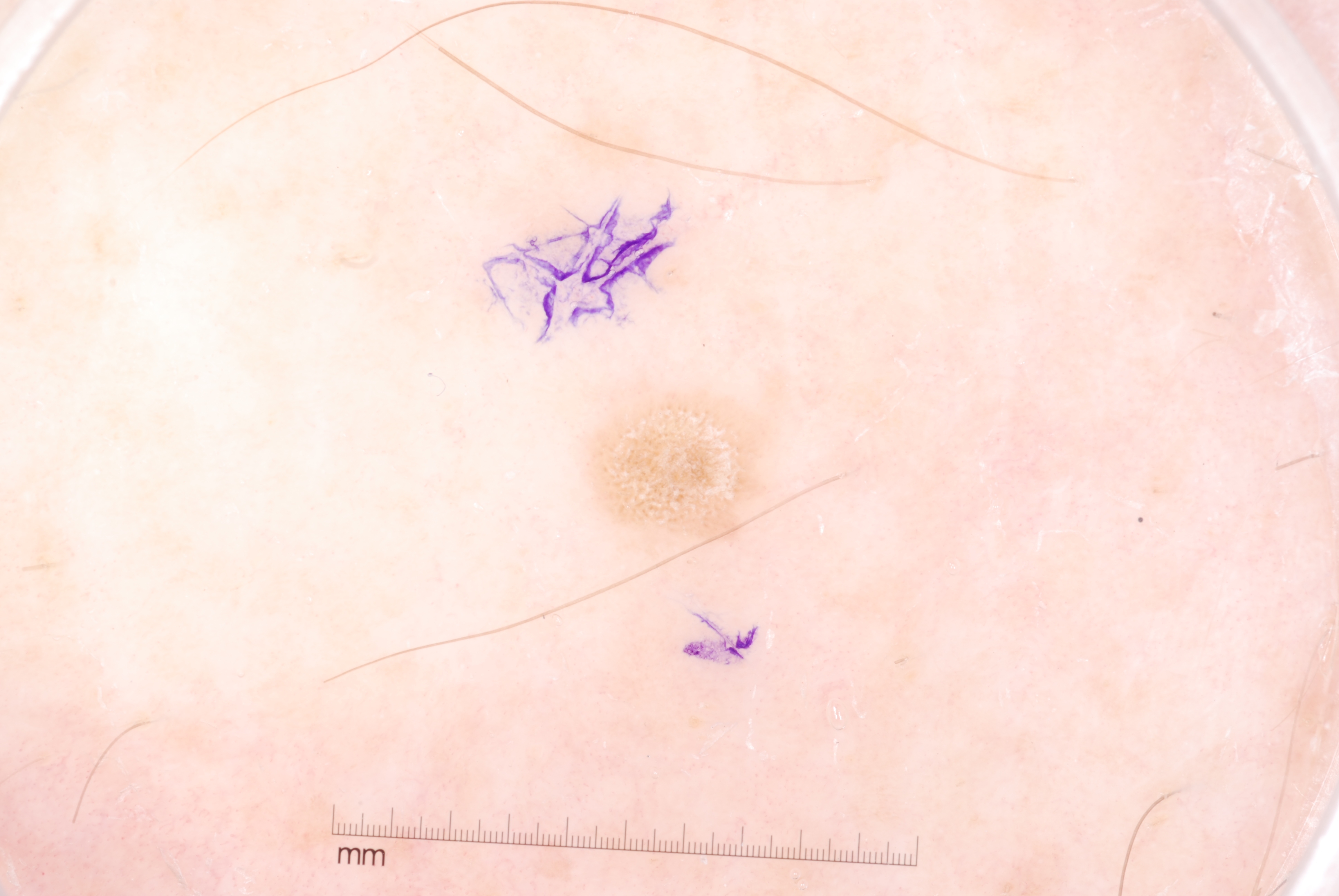Case summary:
– patient: male, in their 70s
– modality: dermoscopy of a skin lesion
– dermoscopic features not present: negative network, milia-like cysts, pigment network, and streaks
– bounding box: 586 385 774 546
– diagnosis: a seborrheic keratosis, a benign lesion